A subject aged 26.
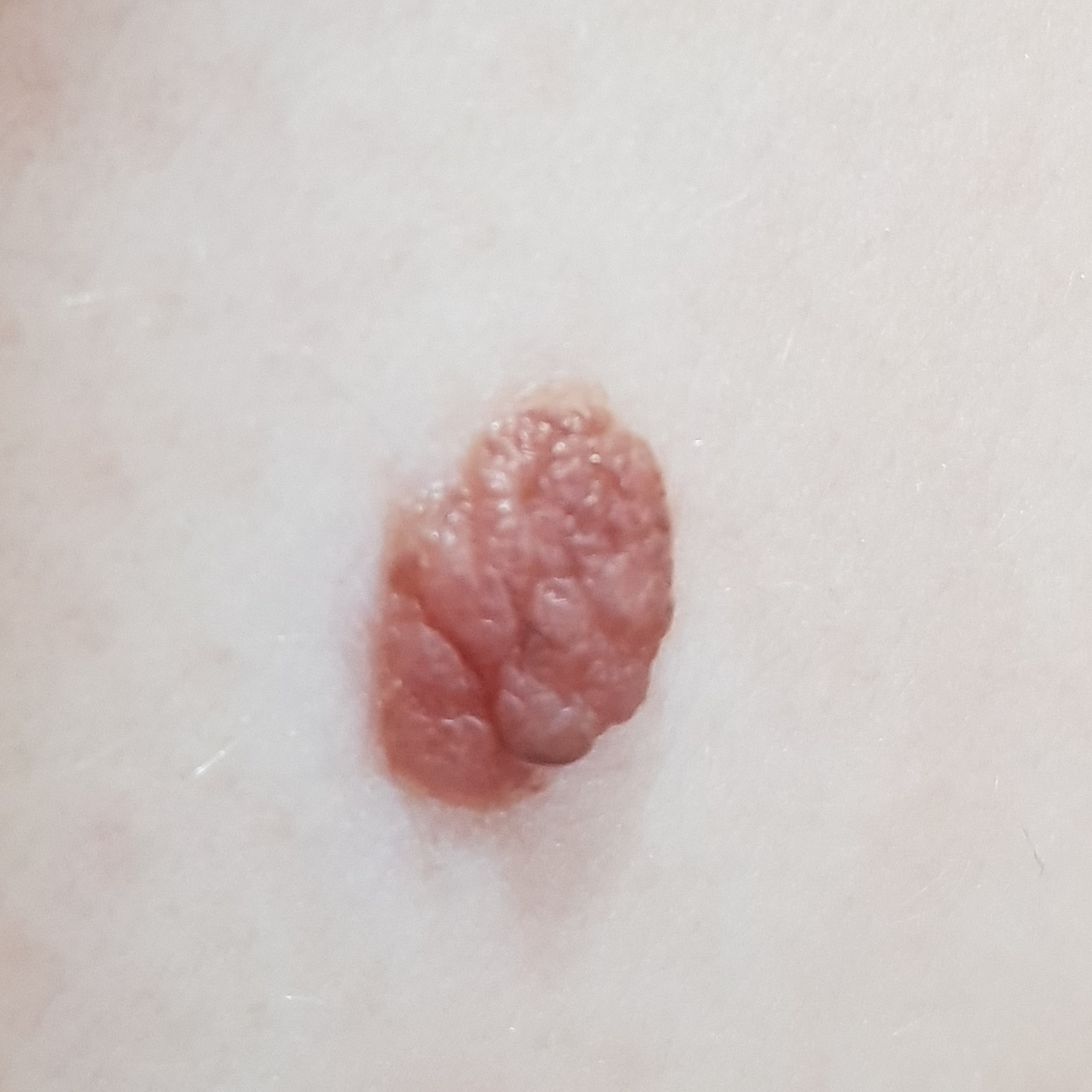region: the back
patient-reported symptoms: growth, elevation
diagnosis: nevus (clinical consensus)